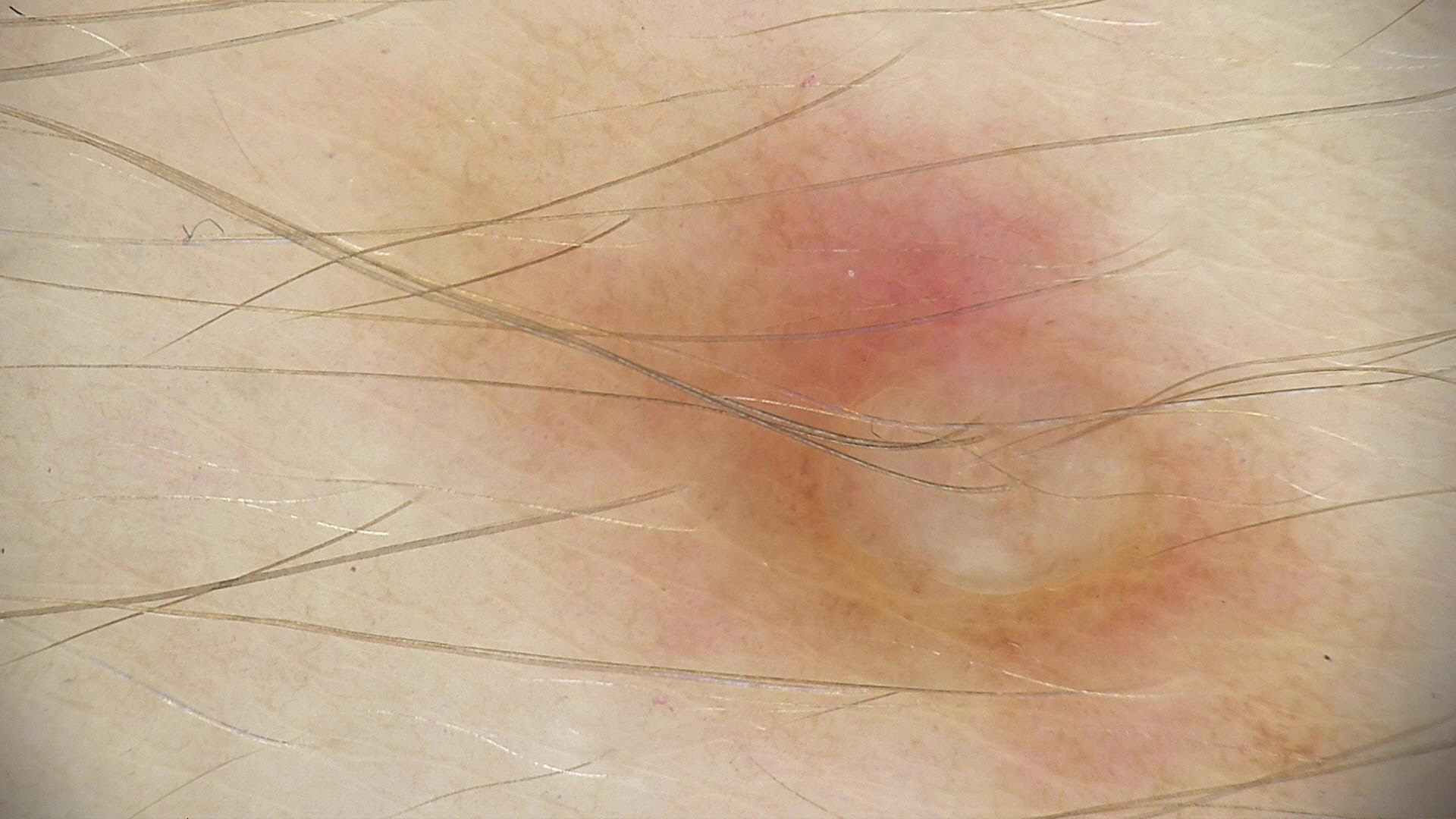<lesion>
<diagnosis>
<name>dermal nevus</name>
<code>db</code>
<malignancy>benign</malignancy>
<super_class>melanocytic</super_class>
<confirmation>expert consensus</confirmation>
</diagnosis>
</lesion>